Recorded as FST IV: 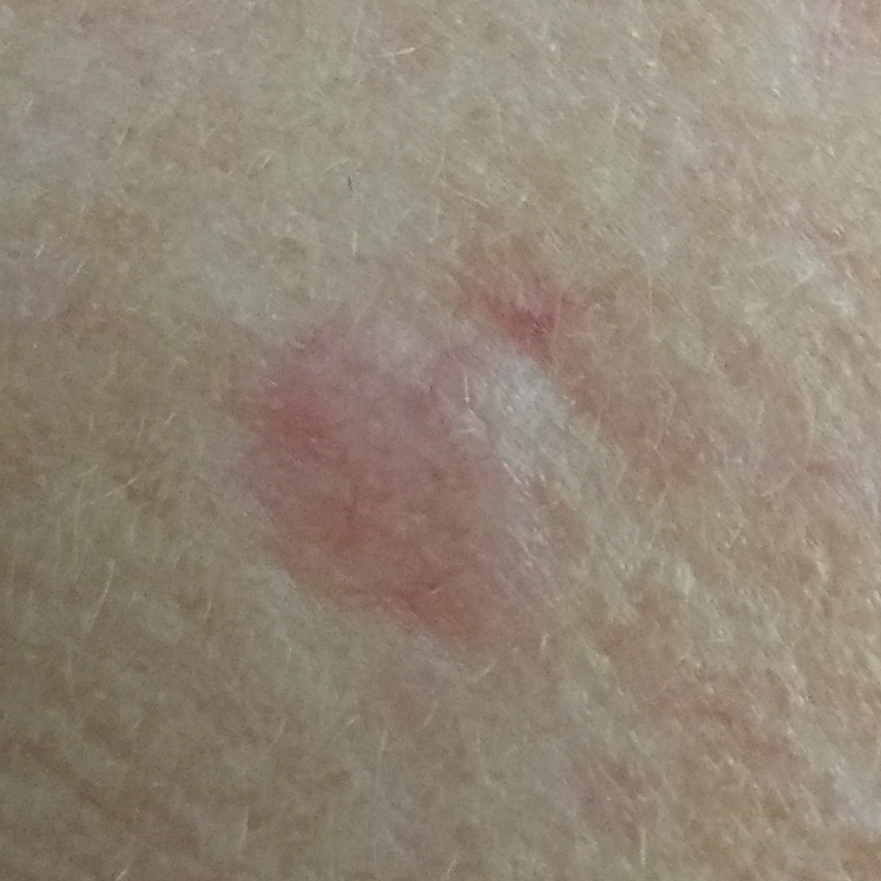location: the face; diameter: 9 × 7 mm; diagnosis: basal cell carcinoma (biopsy-proven).